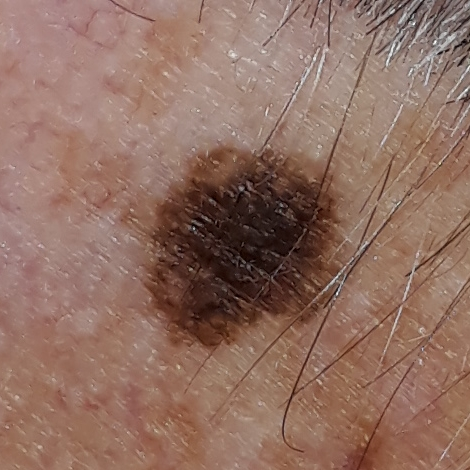* diagnostic label — melanoma (biopsy-proven)